A dermoscopic photograph of a skin lesion.
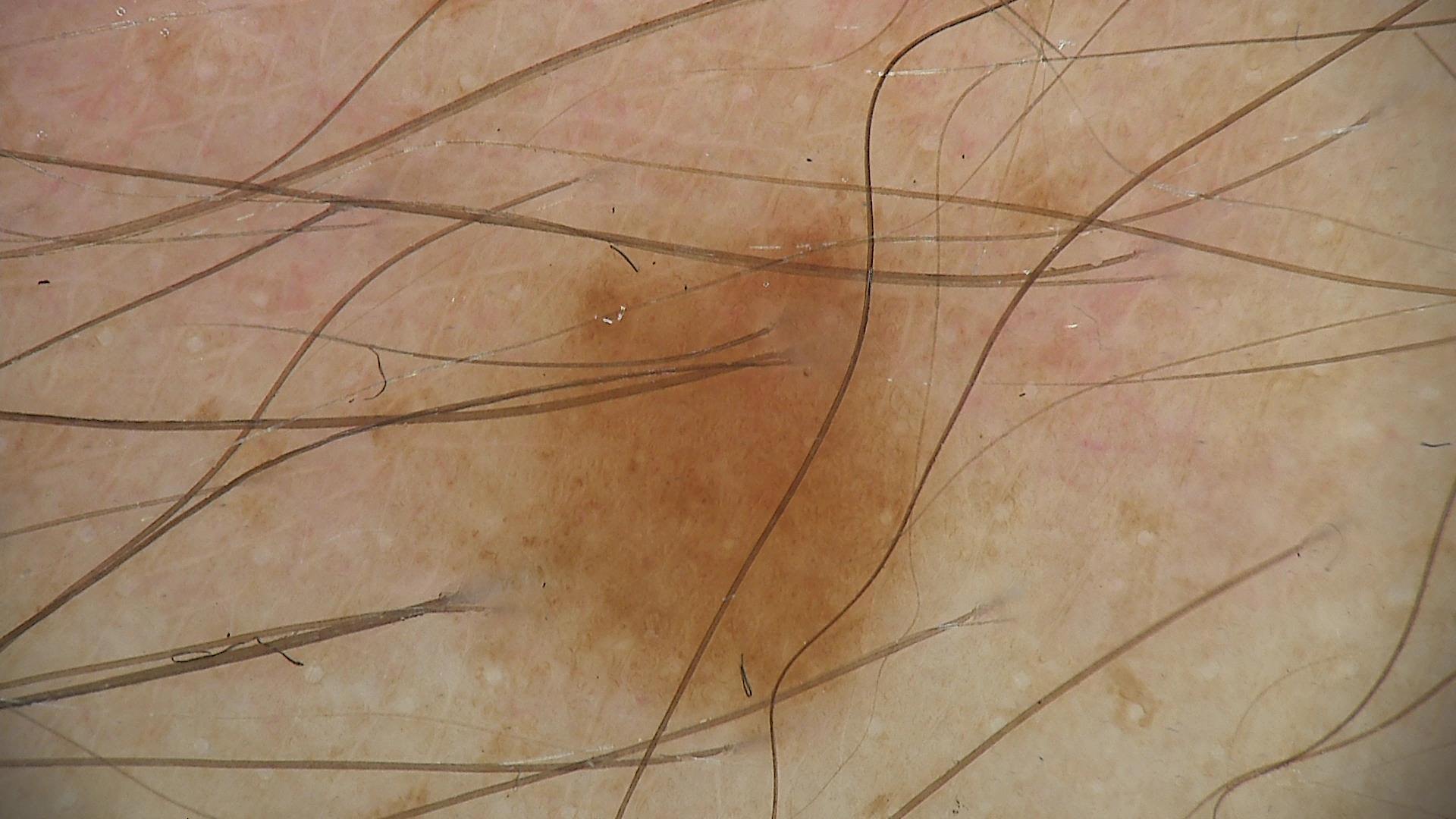Diagnosed as a dysplastic junctional nevus.